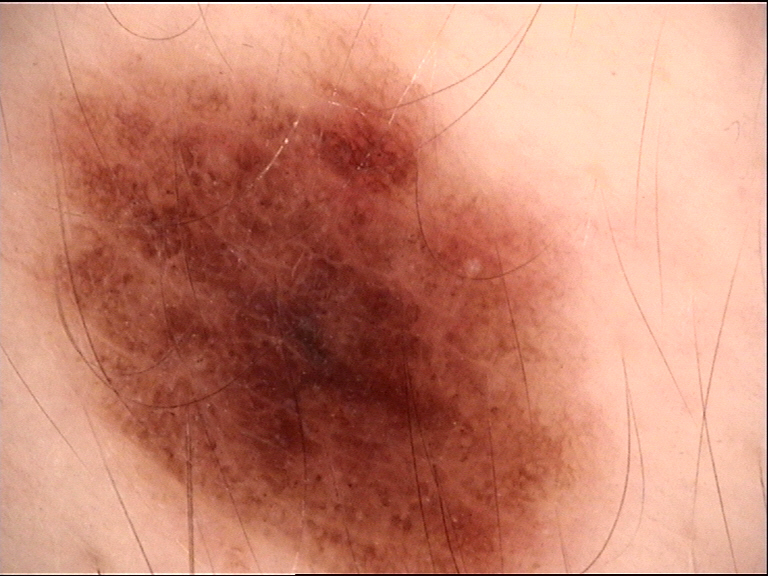modality=dermoscopy; diagnostic label=dysplastic compound nevus (expert consensus).